This image was taken at a distance · the lesion involves the back of the torso and front of the torso: 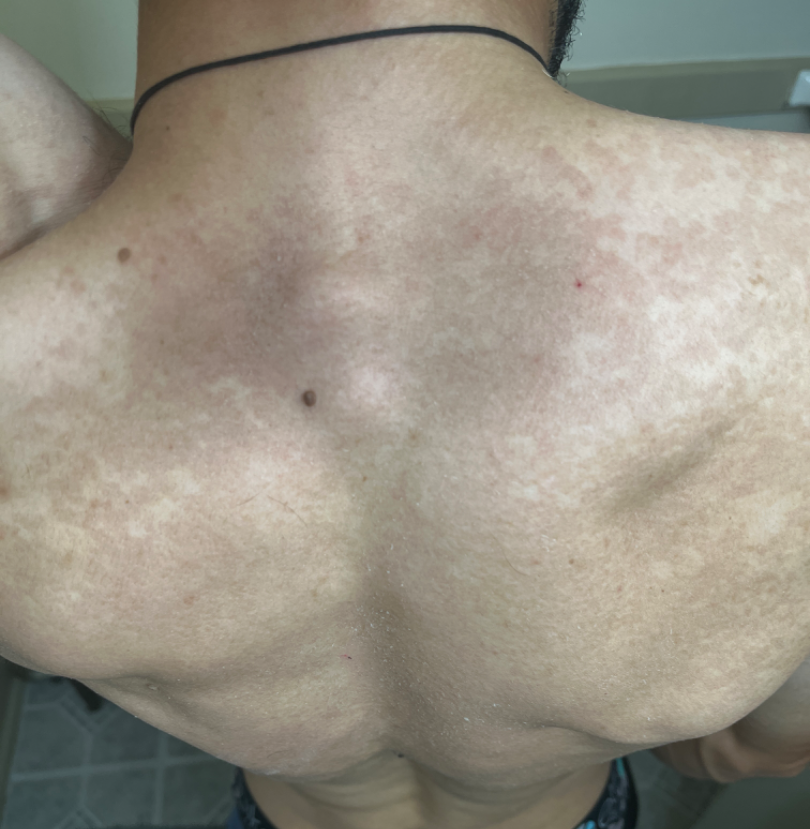Findings:
• diagnostic considerations — most likely Tinea Versicolor